The arm, back of the torso and leg are involved · a close-up photograph · the patient is 40–49, female: 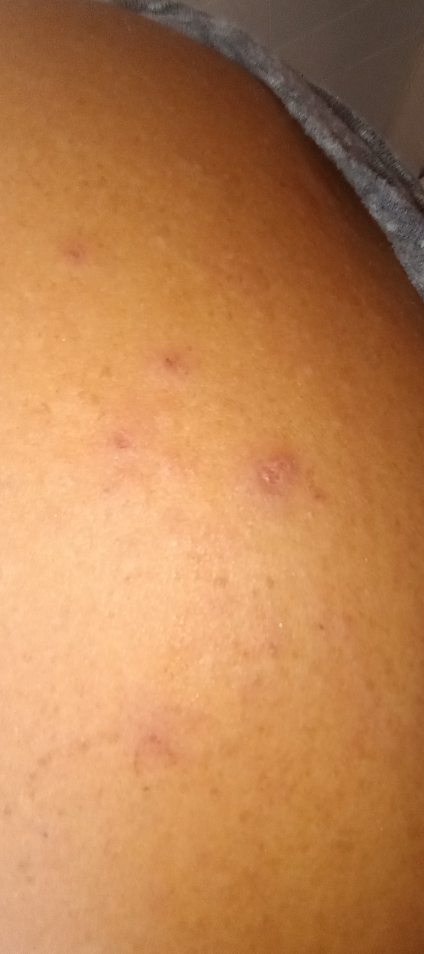Findings: The dermatologist could not determine a likely condition from the photograph alone.